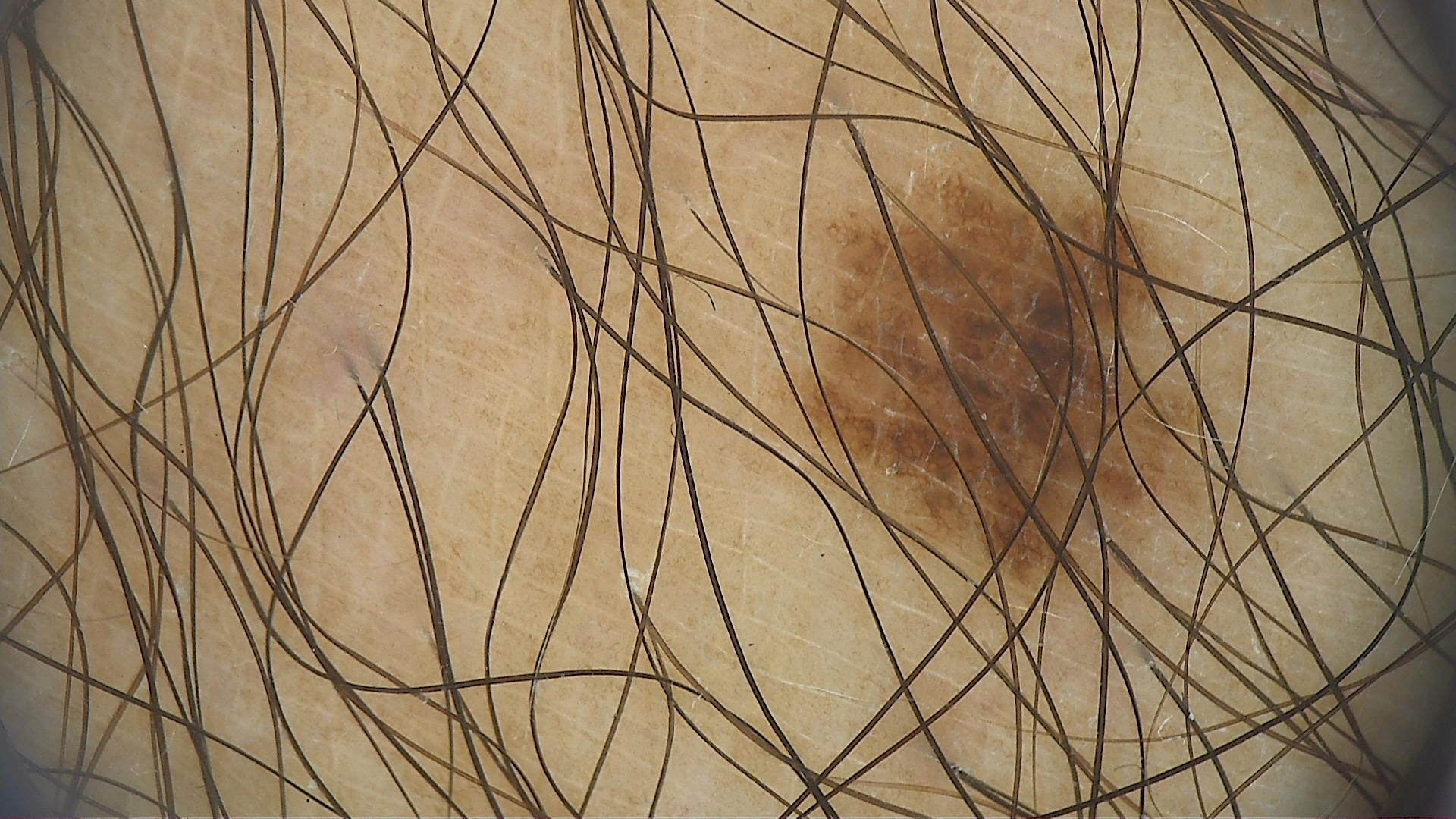<case>
<image>dermoscopy</image>
<diagnosis>
<name>dysplastic junctional nevus</name>
<code>jd</code>
<malignancy>benign</malignancy>
<super_class>melanocytic</super_class>
<confirmation>expert consensus</confirmation>
</diagnosis>
</case>